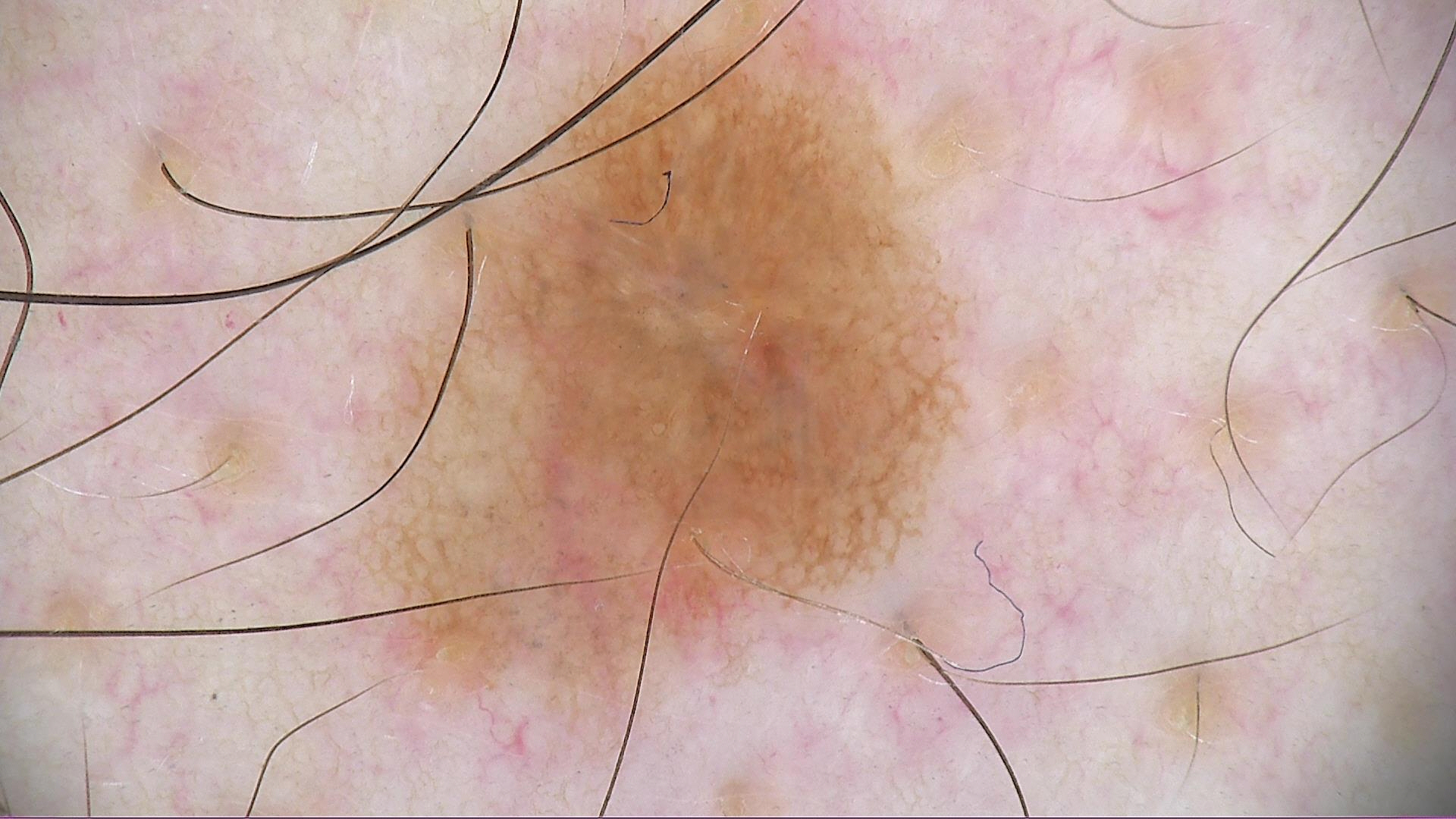Q: What is the diagnosis?
A: compound nevus (expert consensus)